A dermoscopic close-up of a skin lesion.
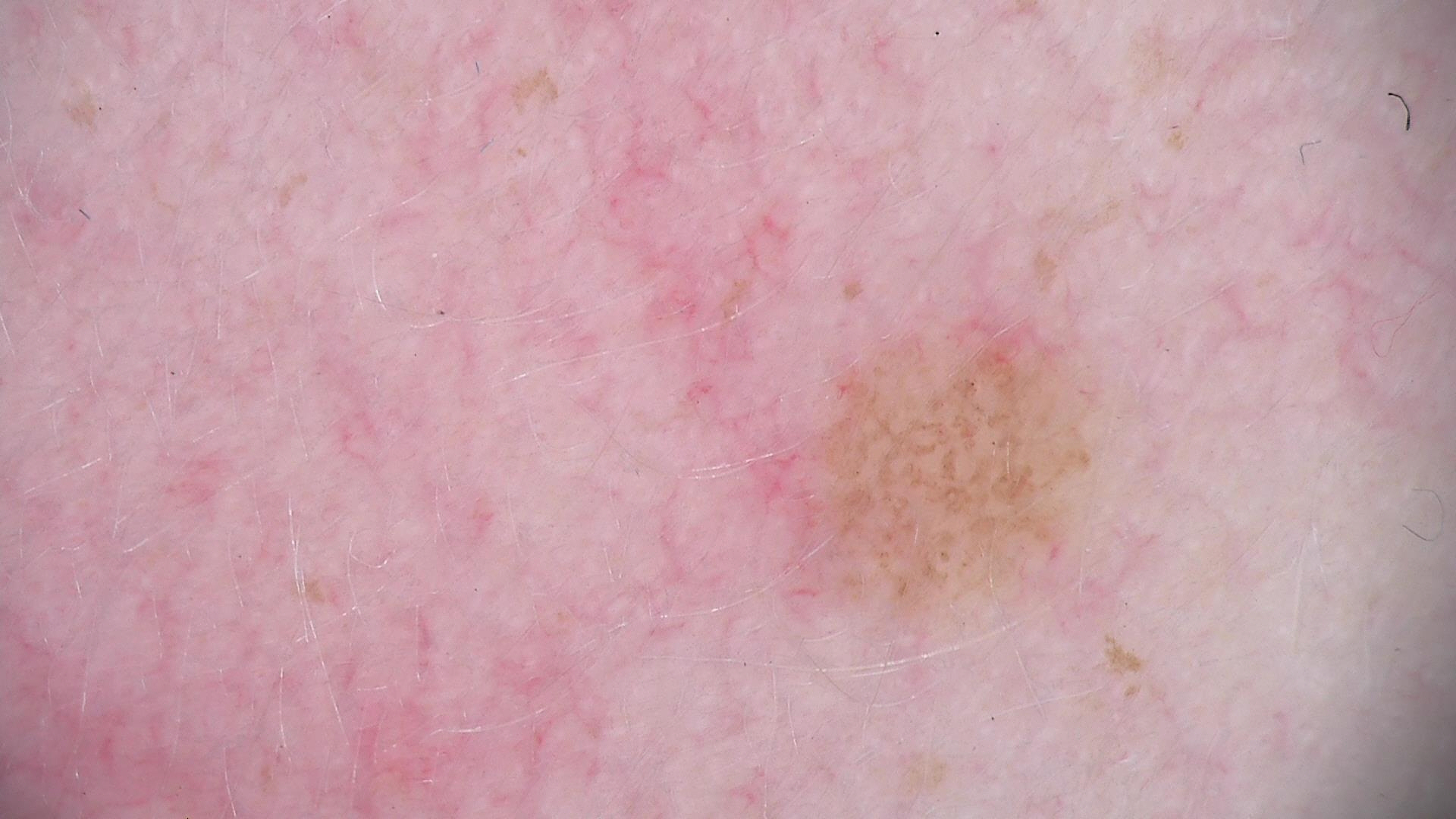Consistent with a banal lesion — a compound nevus.